The arm and front of the torso are involved. An image taken at an angle.
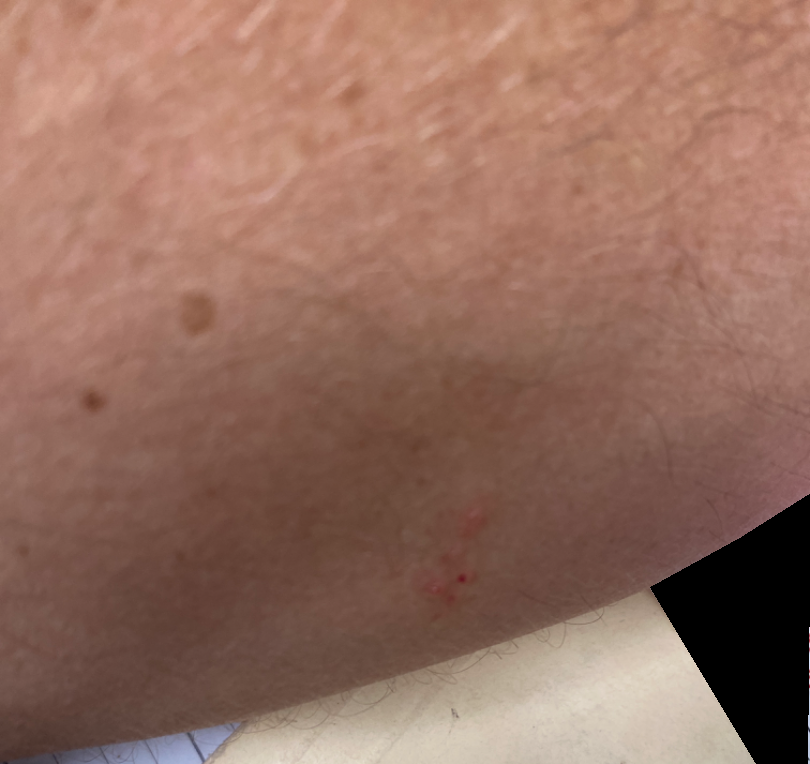The reviewing dermatologist was unable to assign a differential diagnosis from the image.